The affected area is the back of the torso. Close-up view.
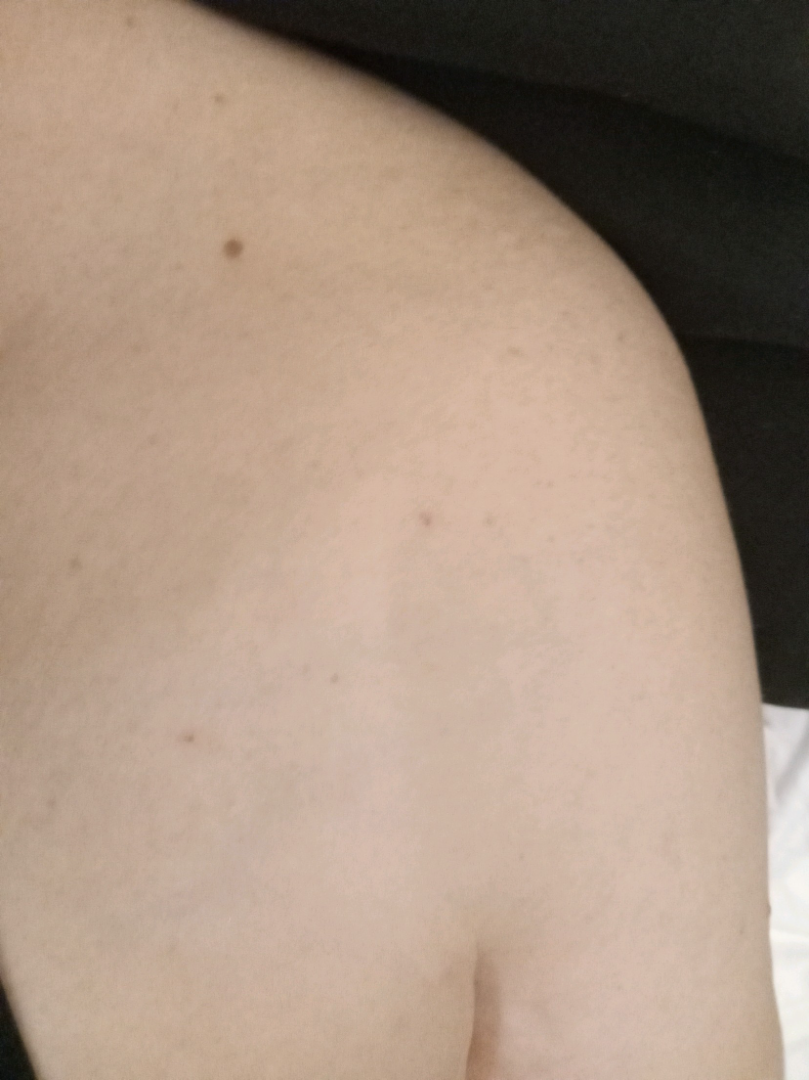Q: Could the case be diagnosed?
A: none discernible